The affected area is the leg. Male contributor, age 18–29. The photograph was taken at an angle — 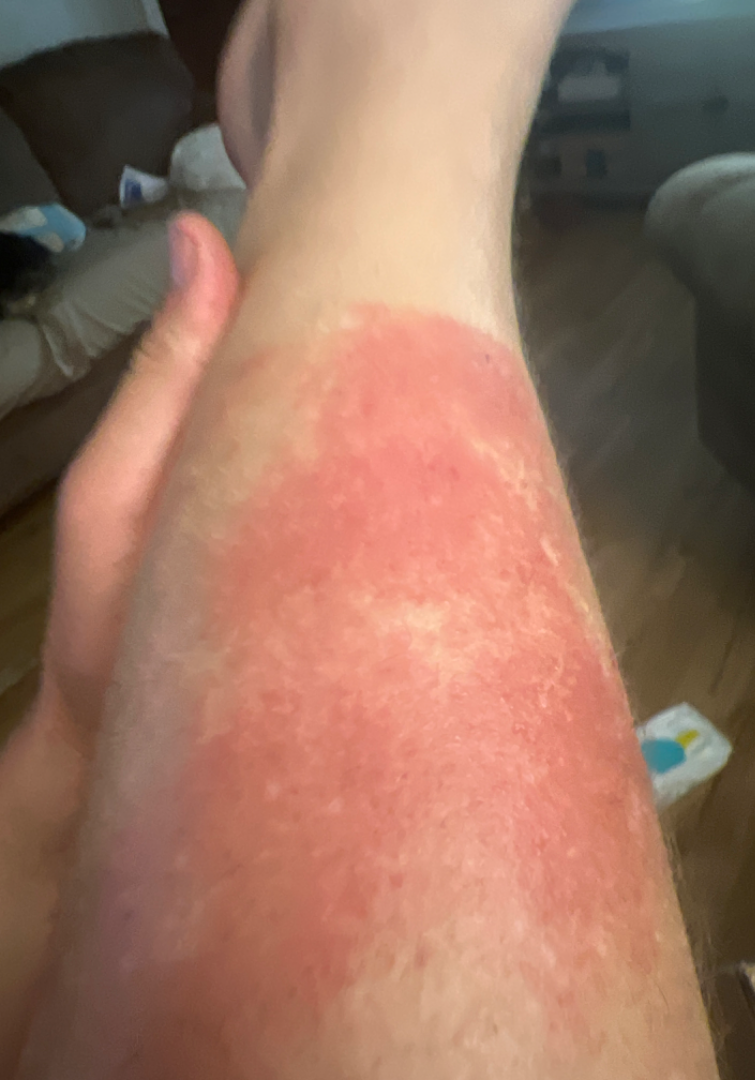described texture: fluid-filled and raised or bumpy | symptom duration: less than one week | clinical impression: most consistent with Acute dermatitis, NOS.